This image was taken at an angle. Located on the arm. The subject is a male aged 40–49 — 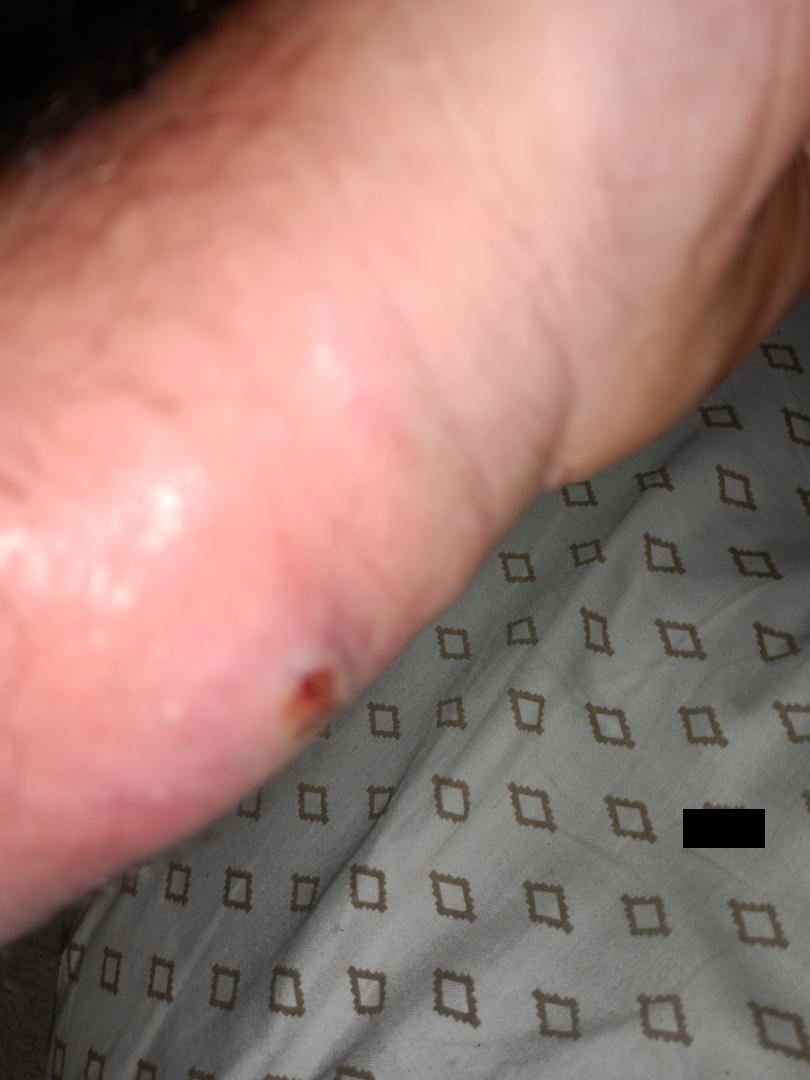The leading consideration is Abscess; lower on the differential is Insect Bite; less probable is Sweet syndrome; less likely is Pyoderma Gangrenosum; a remote consideration is Skin and soft tissue atypical mycobacterial infection; a more distant consideration is Snake bite - wound.